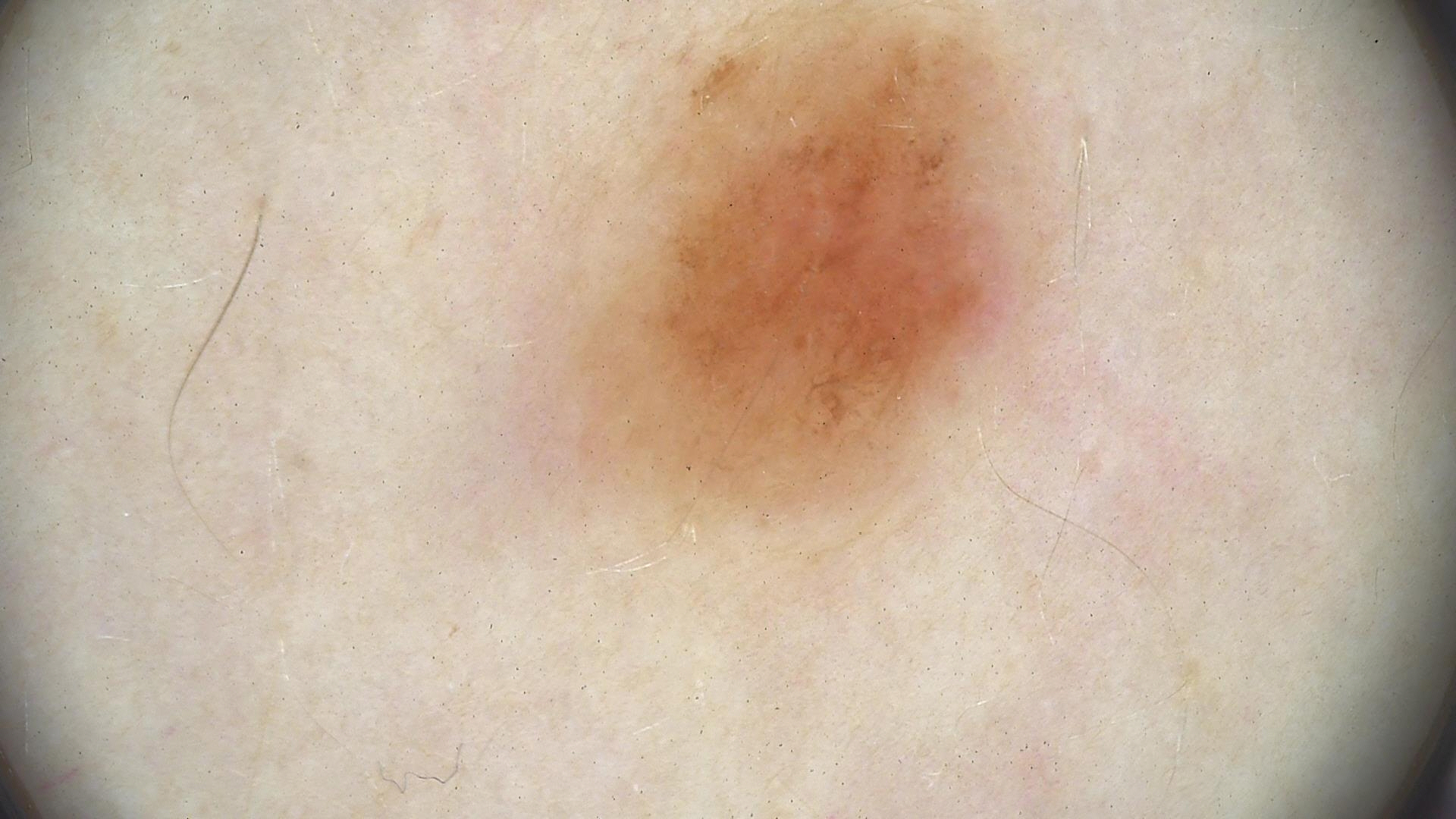Dermoscopy of a skin lesion. Classified as a dysplastic junctional nevus.